The patient describes having a moderate number of moles; referred with a clinical suspicion of basal cell carcinoma; on a questionnaire the patient reported a prior organ transplant and immunosuppression; a skin lesion imaged with a dermatoscope:
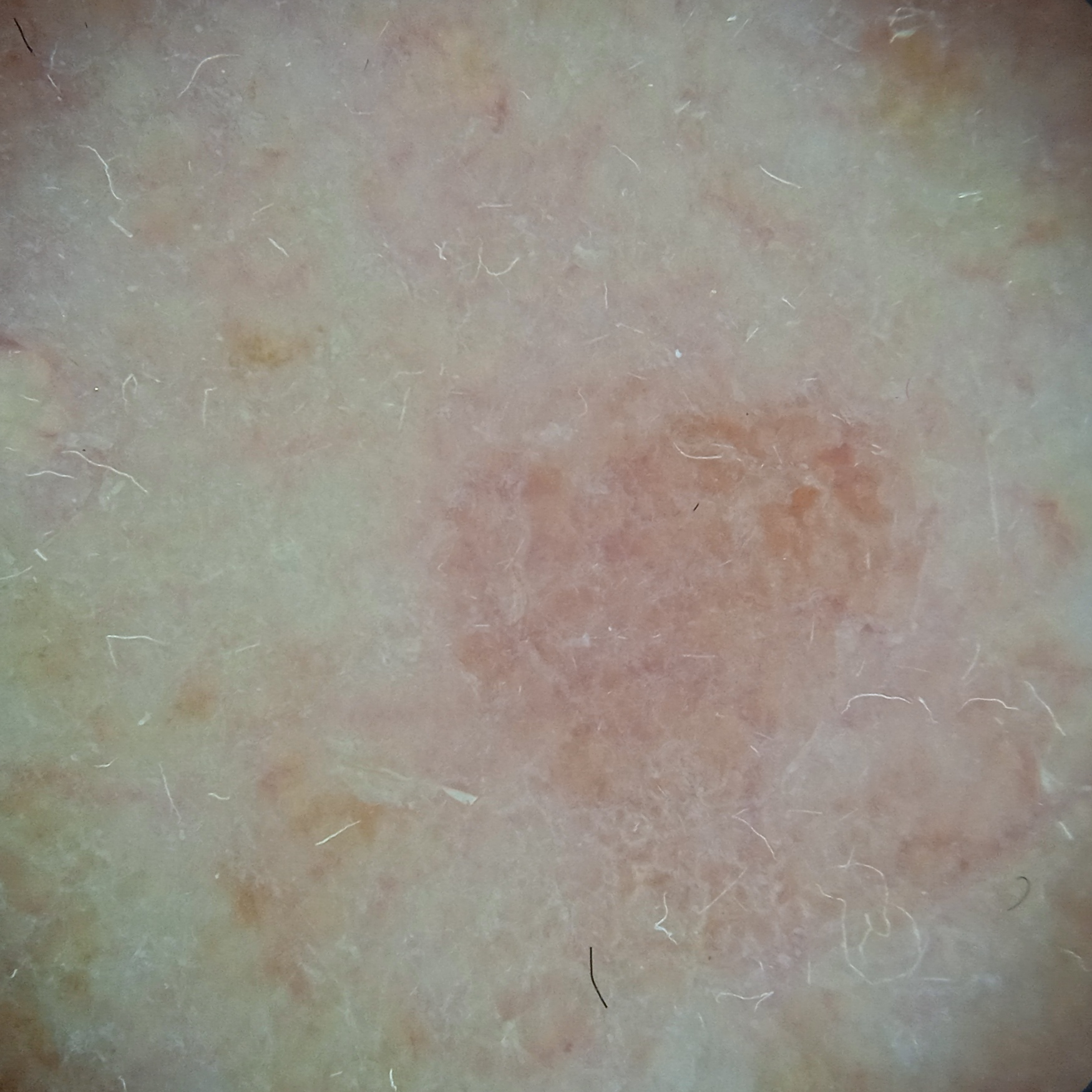The lesion is located on the face.
The dermatologists' assessment was an actinic keratosis.